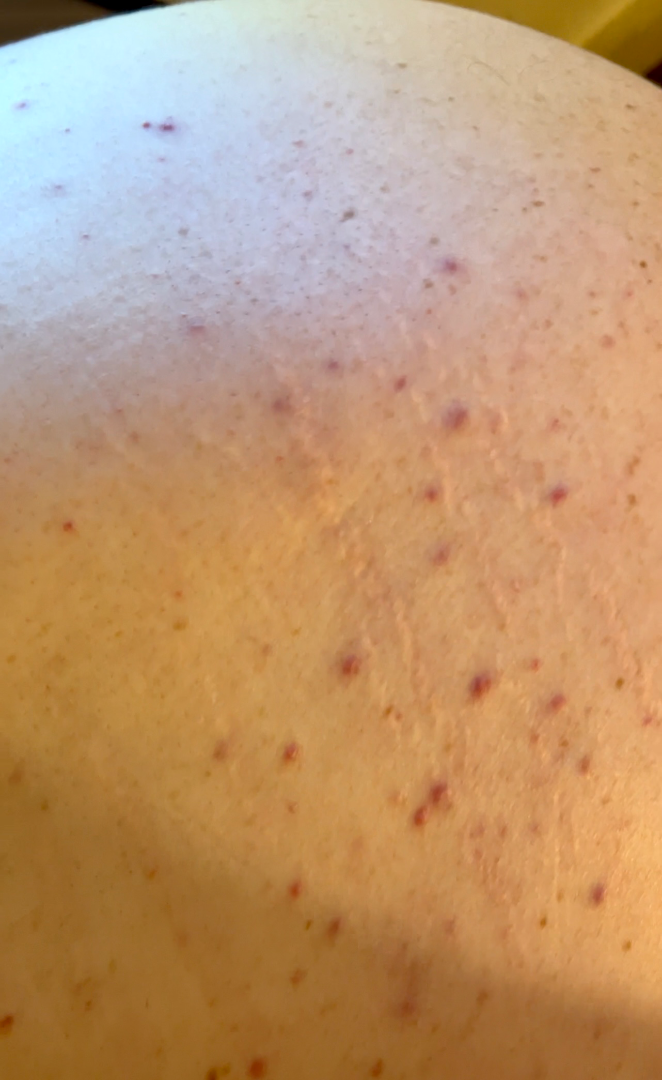One reviewing dermatologist: most consistent with Leukocytoclastic Vasculitis; also on the differential is Pityriasis lichenoides; also consider Folliculitis.